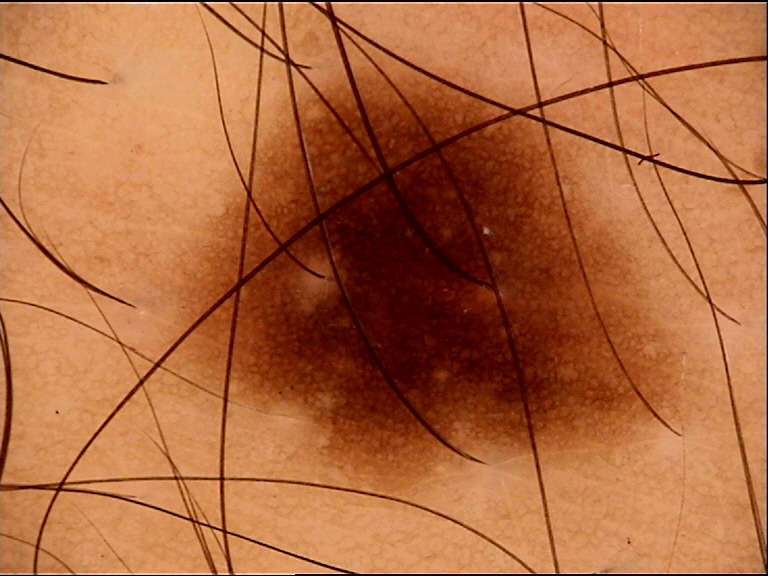A dermoscopic image of a skin lesion. The diagnostic label was a banal lesion — a junctional nevus.